The patient says their skin tans without first burning; a clinical photograph showing a skin lesion; a moderate number of moles by the patient's own estimate; imaged for a research study, with no referral diagnosis recorded; the patient reports a personal history of skin cancer, a personal history of cancer, and a family history of skin cancer; a female patient 58 years old:
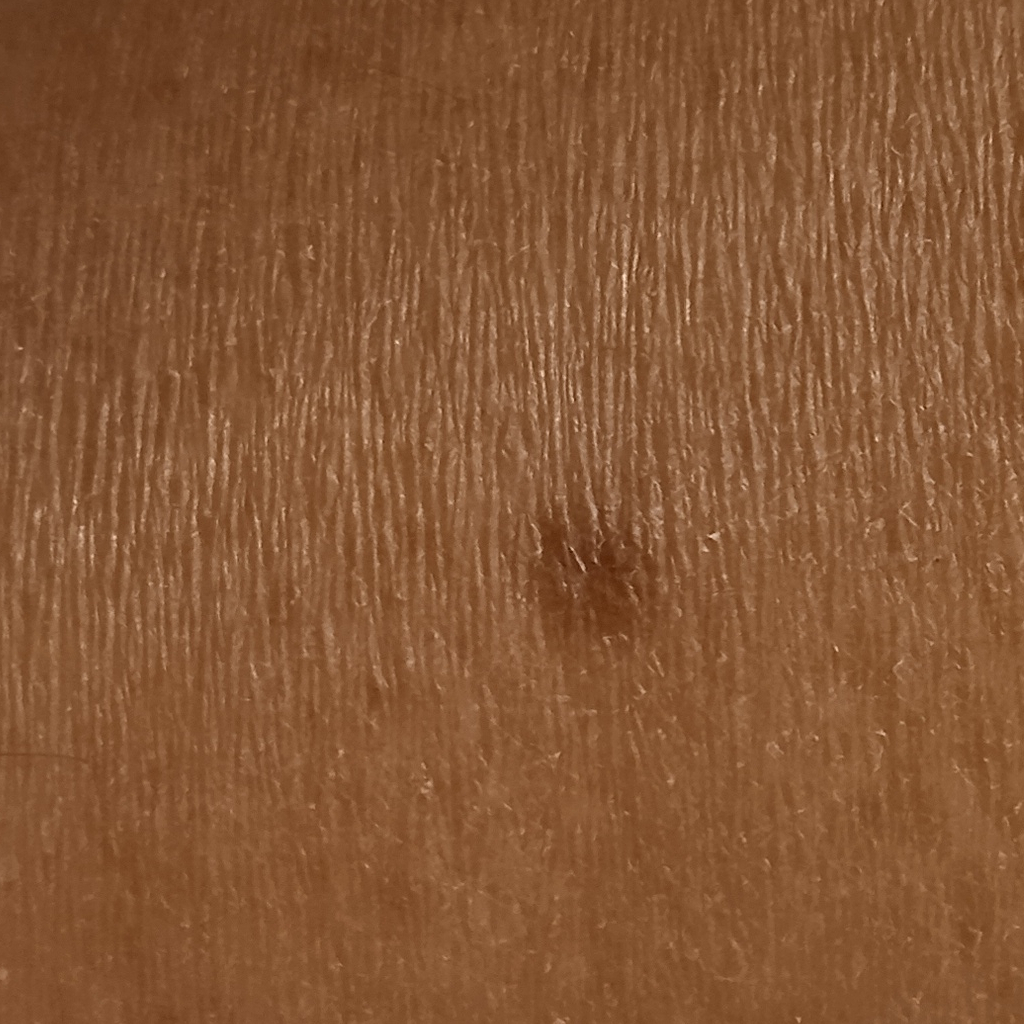Q: Lesion size?
A: 5.2 mm
Q: What was the diagnosis?
A: dermatofibroma (dermatologist consensus)